Dermoscopy of a skin lesion:
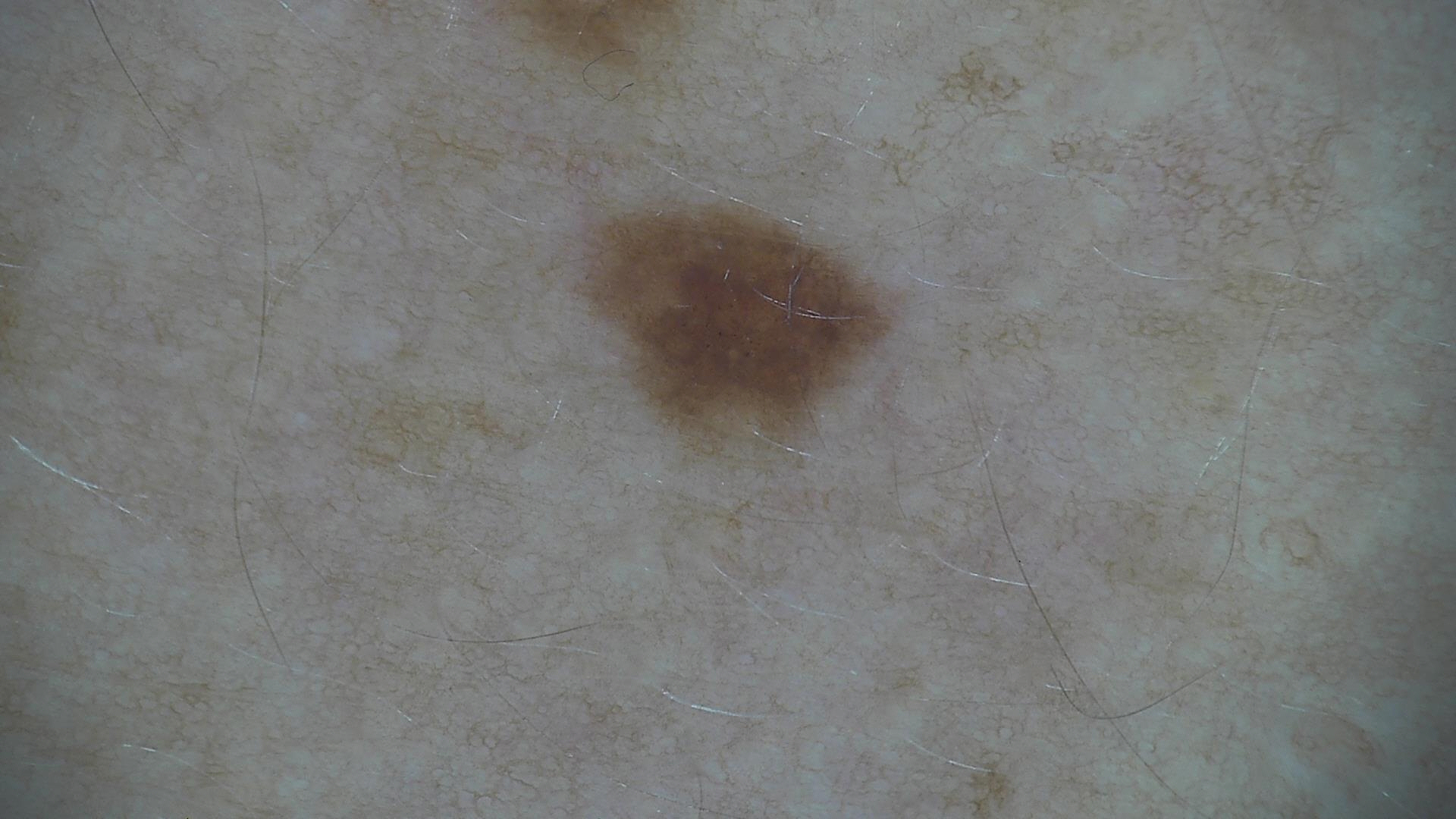| key | value |
|---|---|
| class | dysplastic junctional nevus (expert consensus) |